Close-up view, located on the palm, the subject is male, the patient considered this skin that appeared healthy to them:
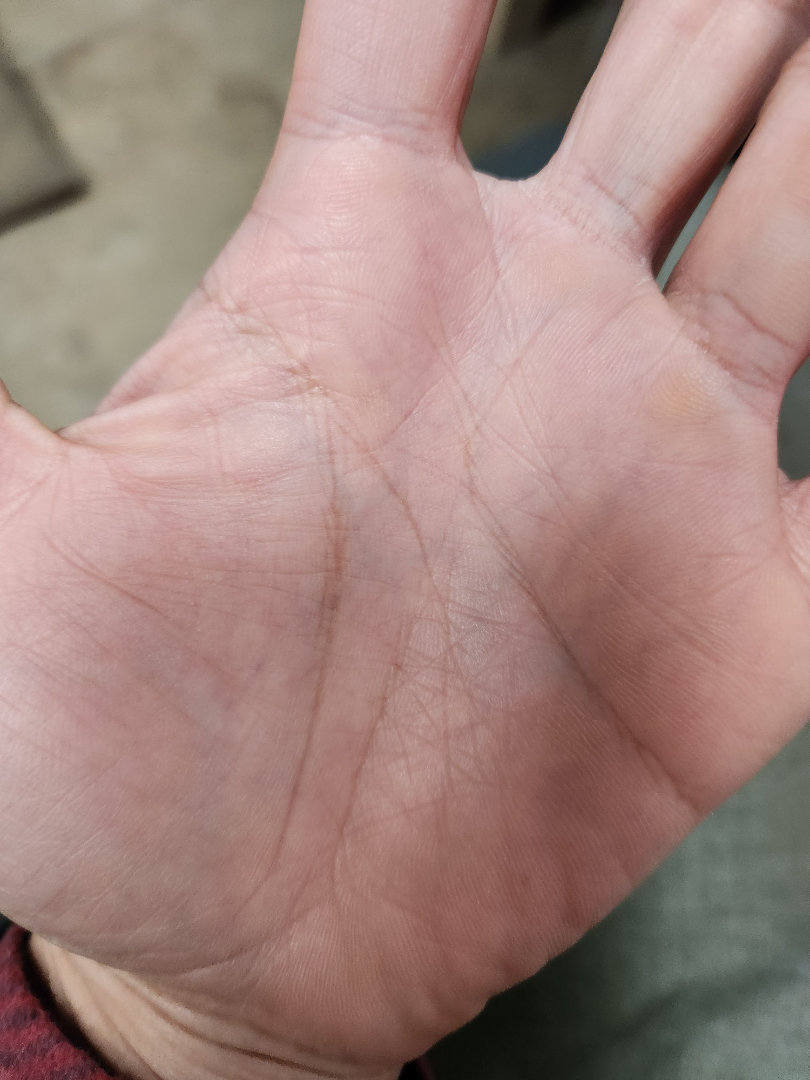{
  "differential": {
    "tied_lead": [
      "hyperlinear palm",
      "Eczema"
    ]
  }
}